A dermoscopic close-up of a skin lesion.
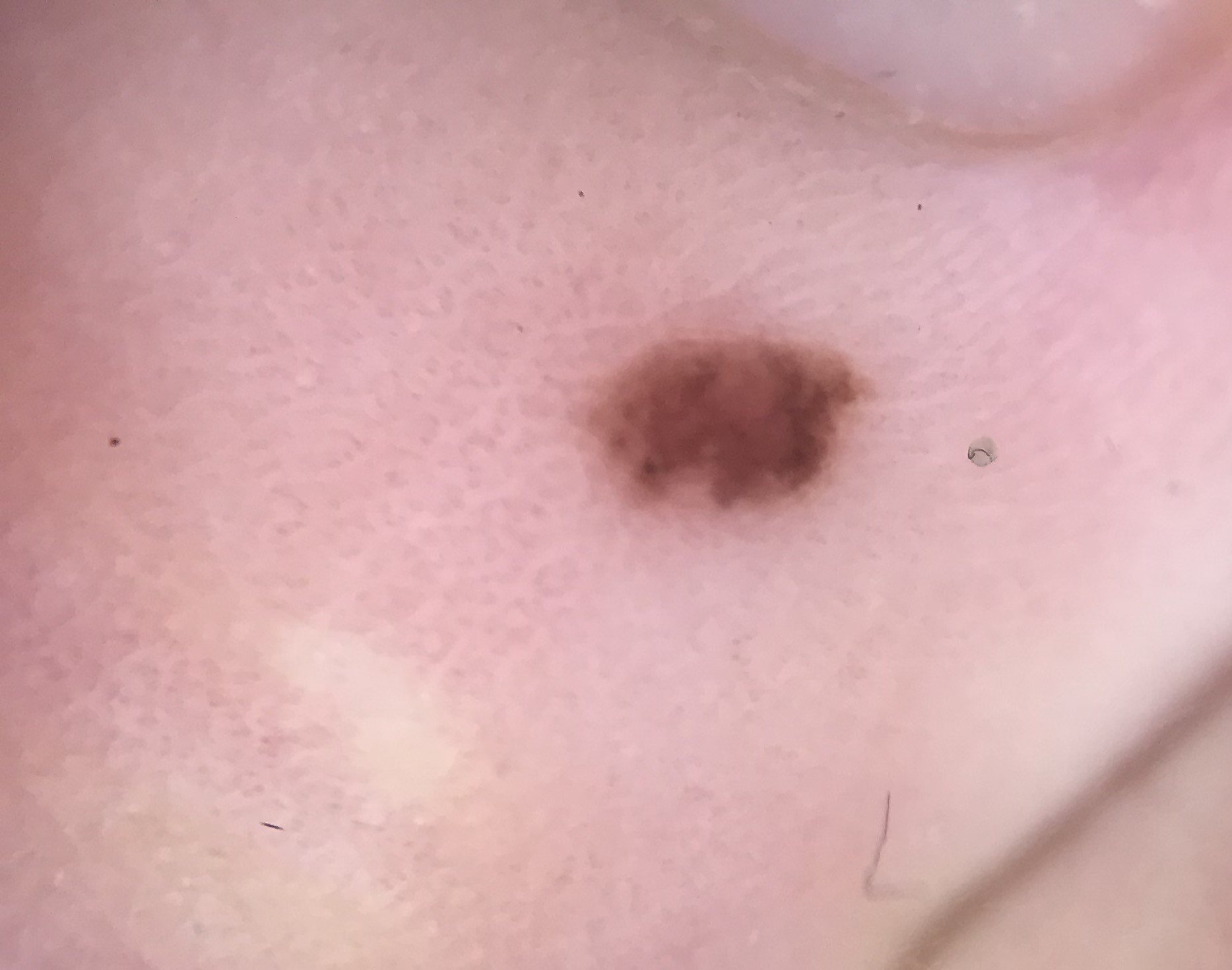Classified as a banal lesion — an acral compound nevus.